A dermoscopic photograph of a skin lesion.
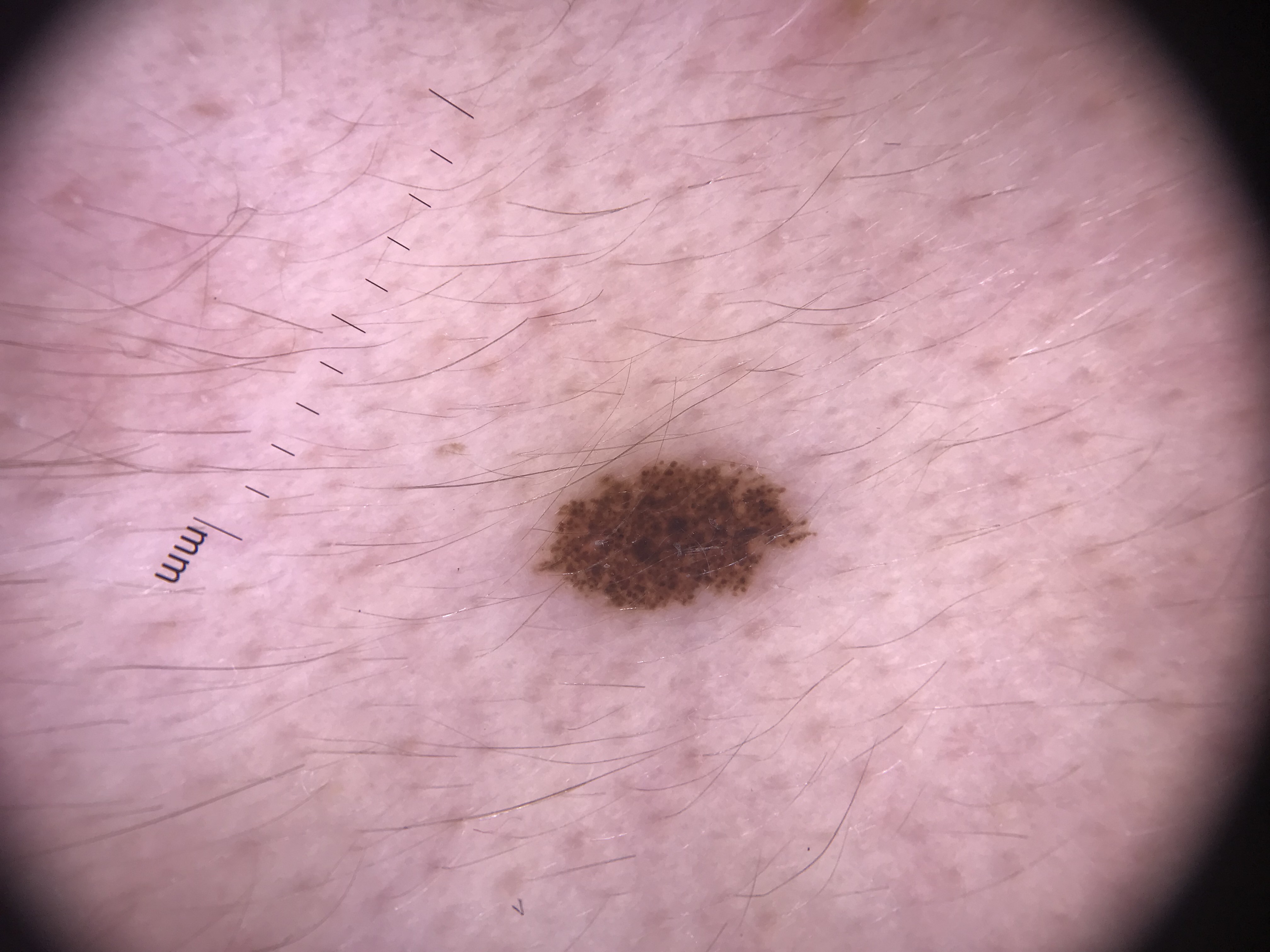Impression: The diagnosis was a dysplastic junctional nevus.